A dermoscopic photograph of a skin lesion:
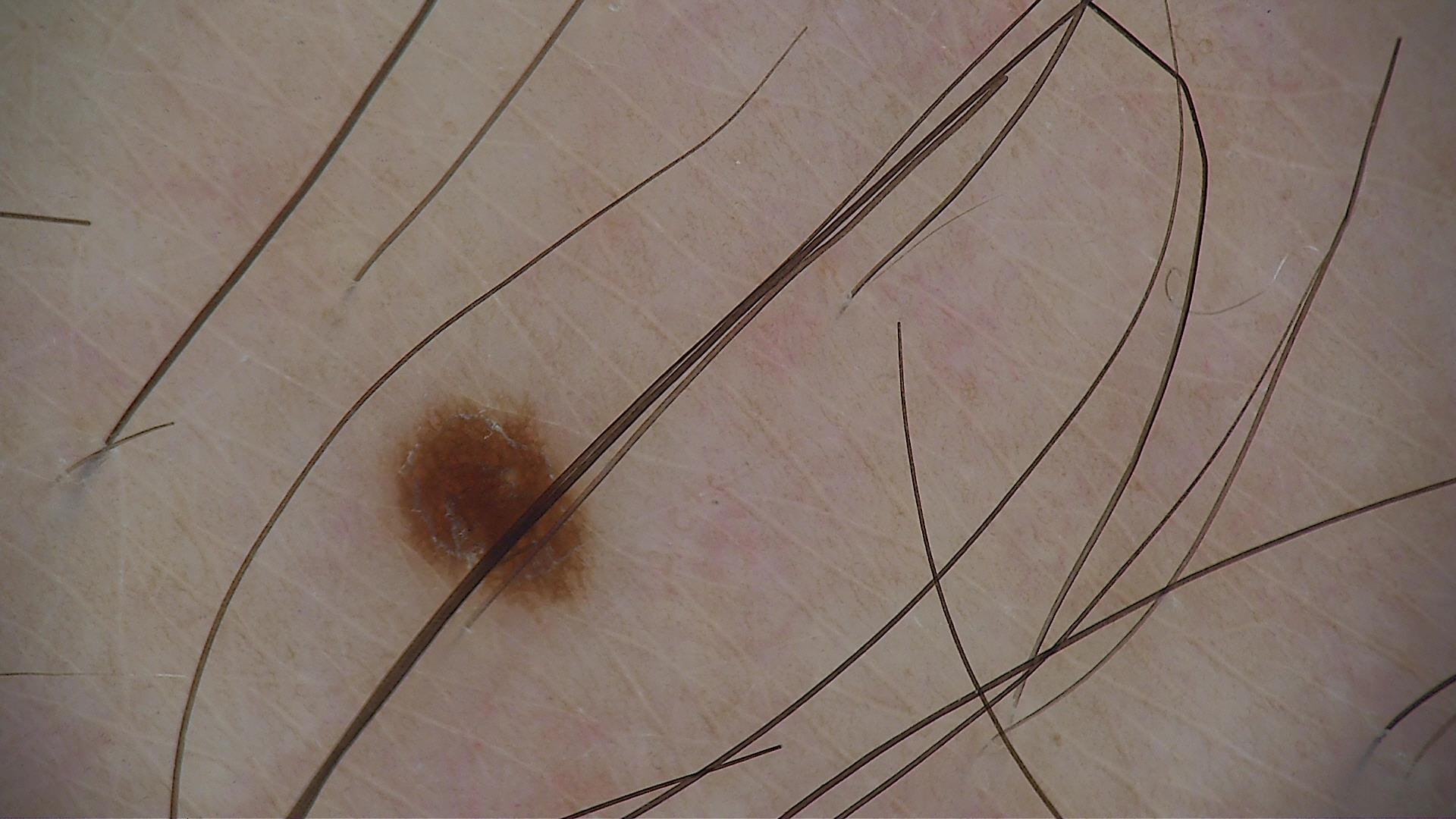Consistent with a benign lesion — a dysplastic junctional nevus.